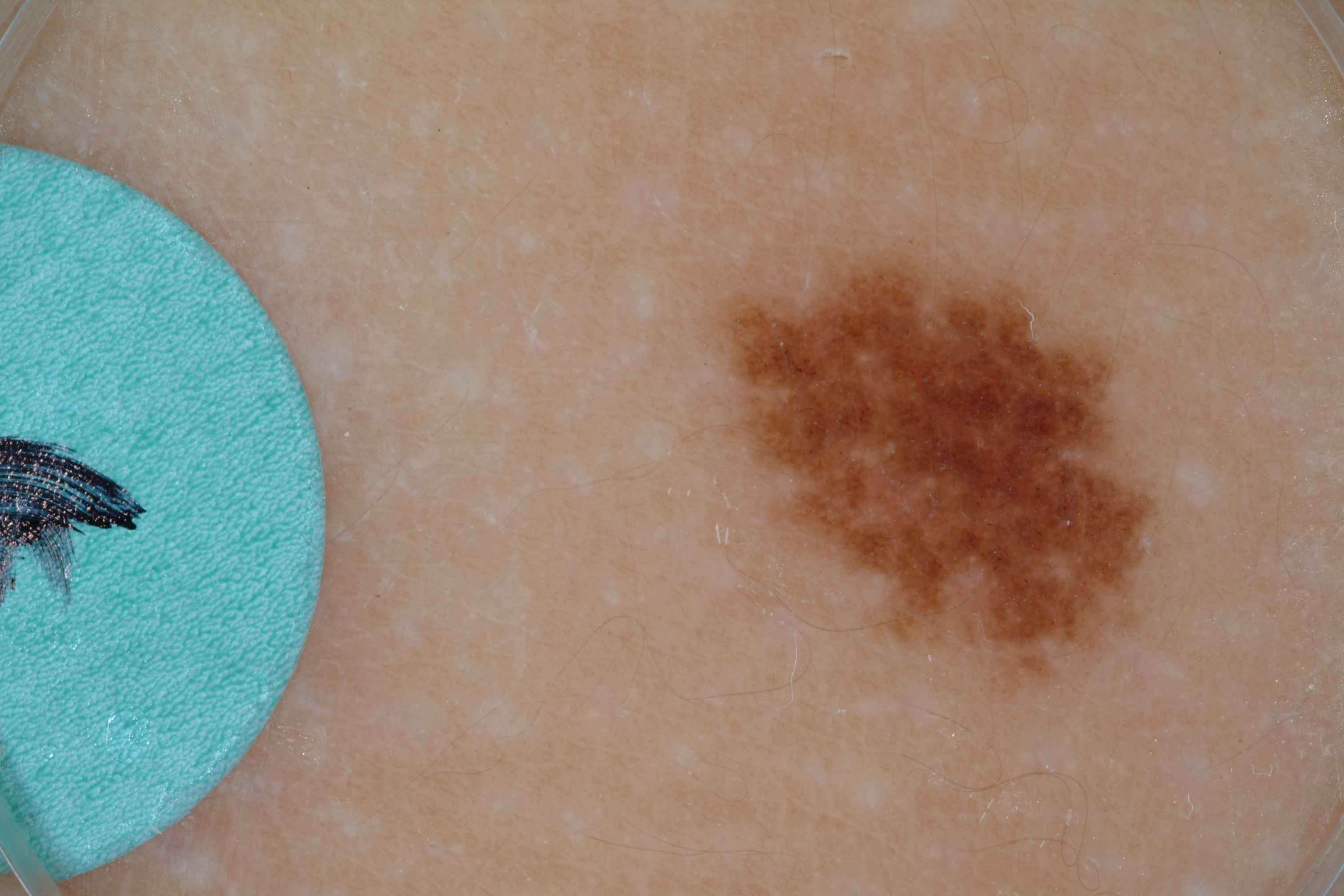Q: Patient demographics?
A: male, aged 8 to 12
Q: What kind of image is this?
A: dermatoscopic image of a skin lesion
Q: Lesion extent?
A: moderate
Q: Where is the lesion located?
A: <box>713, 239, 1161, 702</box>
Q: What does dermoscopy show?
A: pigment network and globules; absent: negative network, streaks, and milia-like cysts
Q: What is this lesion?
A: a melanocytic nevus